The condition has been present for one to four weeks, the patient indicates associated joint pain and fatigue, the patient is a female aged 30–39, the lesion is described as raised or bumpy and fluid-filled, this image was taken at an angle, the patient indicates bothersome appearance — 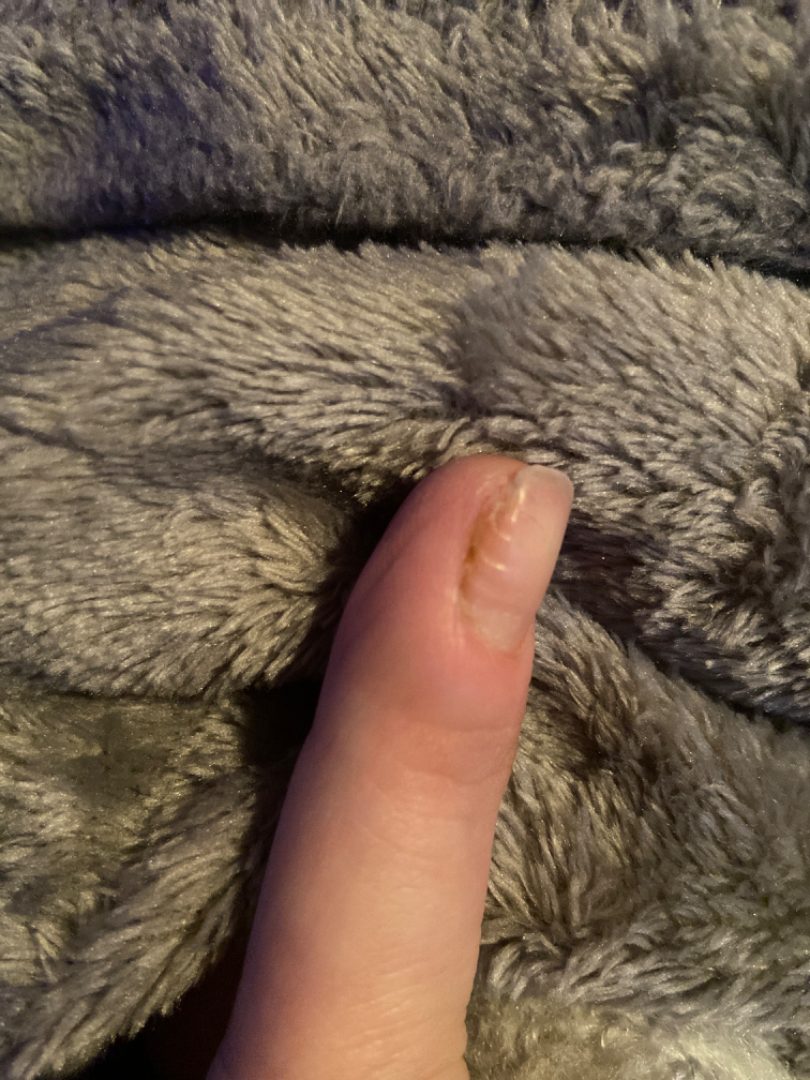Assessment: Most consistent with Nail dystrophy; an alternative is Nail pitting; also raised was Nail dystrophy due to trauma; a more distant consideration is Paronychia; less probable is Onychomycosis.